Dermoscopy of a skin lesion: 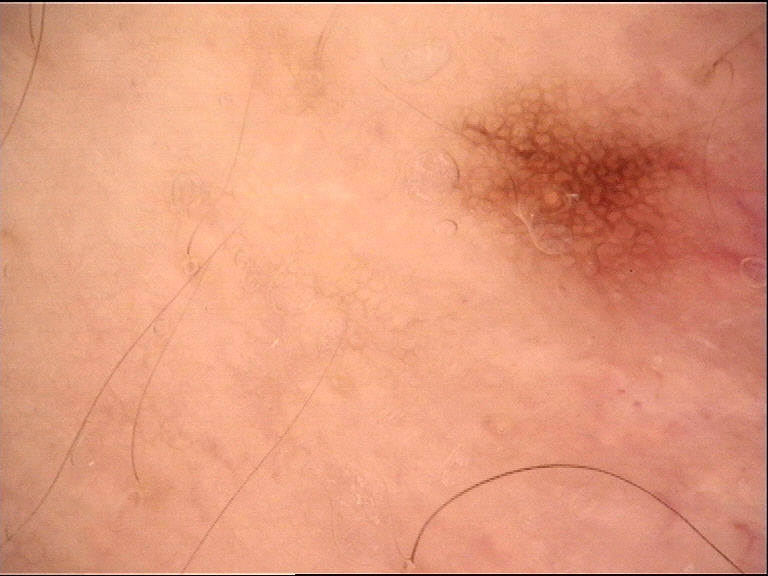The diagnostic label was a benign lesion — a dysplastic junctional nevus.